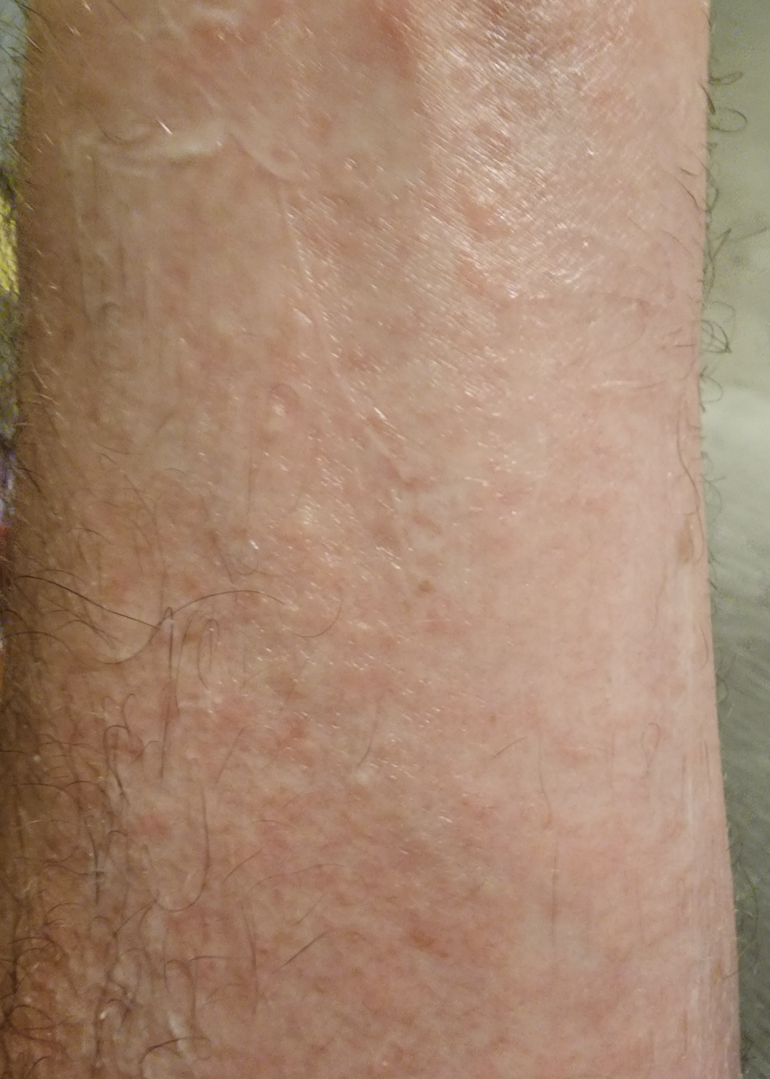Notes:
– differential — Eczema (primary); Allergic Contact Dermatitis (considered); Viral Exanthem (remote); Drug Rash (remote)